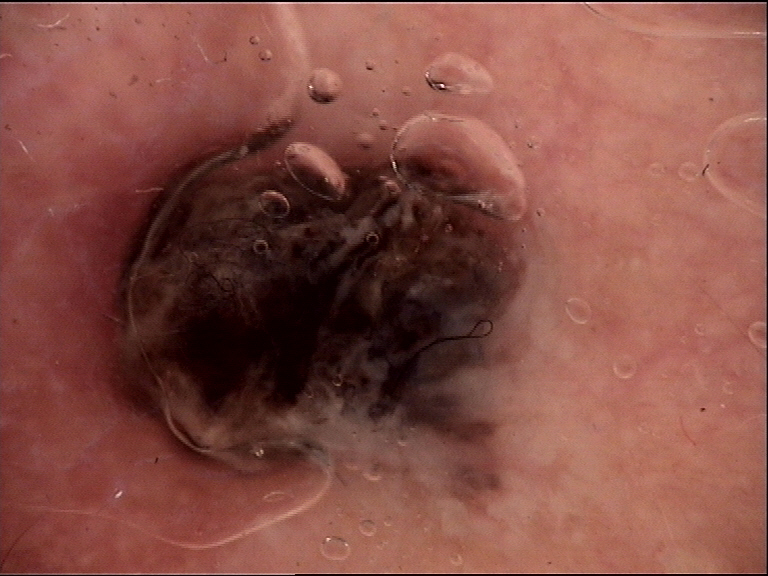Confirmed on histopathology as a melanoma.